Symptoms reported: itching, self-categorized by the patient as a rash, the patient is a male aged 18–29, close-up view, the lesion is described as raised or bumpy, skin tone: Fitzpatrick II; lay reviewers estimated Monk Skin Tone 1 (US pool) or 2 (India pool), the affected area is the back of the hand, present for one to four weeks:
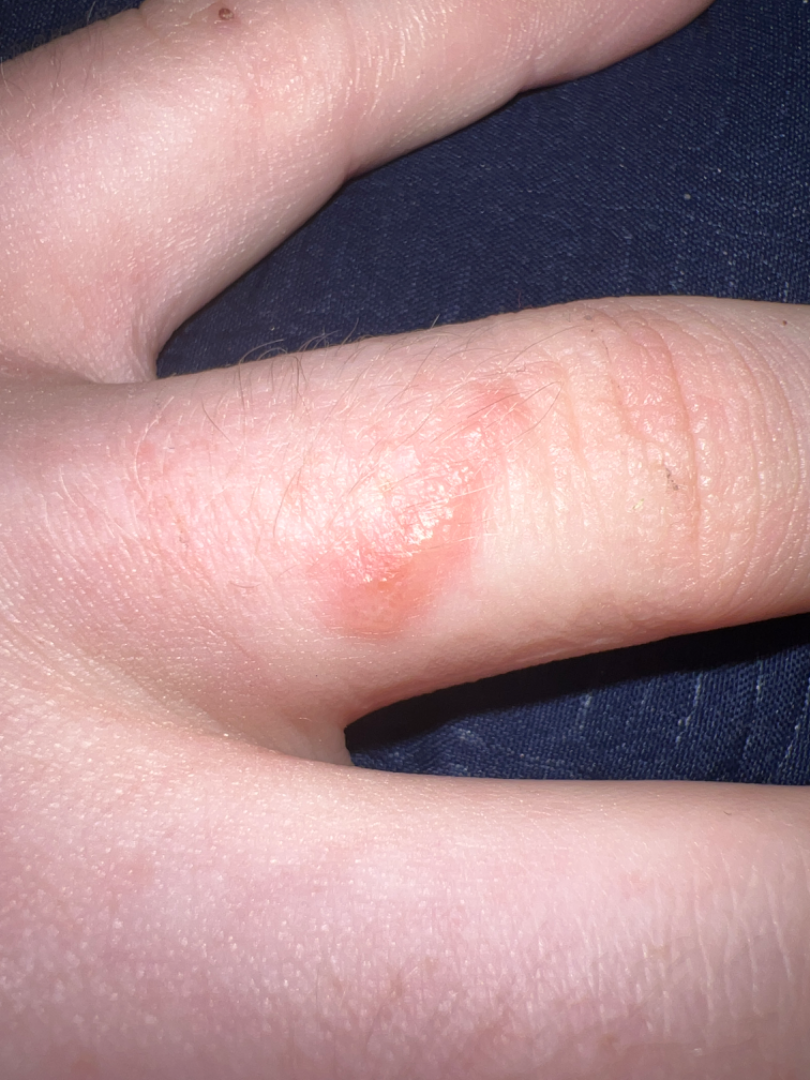Impression:
On dermatologist assessment of the image, Photodermatitis (weight 0.33); Contact dermatitis caused by Rhus diversiloba (weight 0.33); Allergic Contact Dermatitis (weight 0.33).